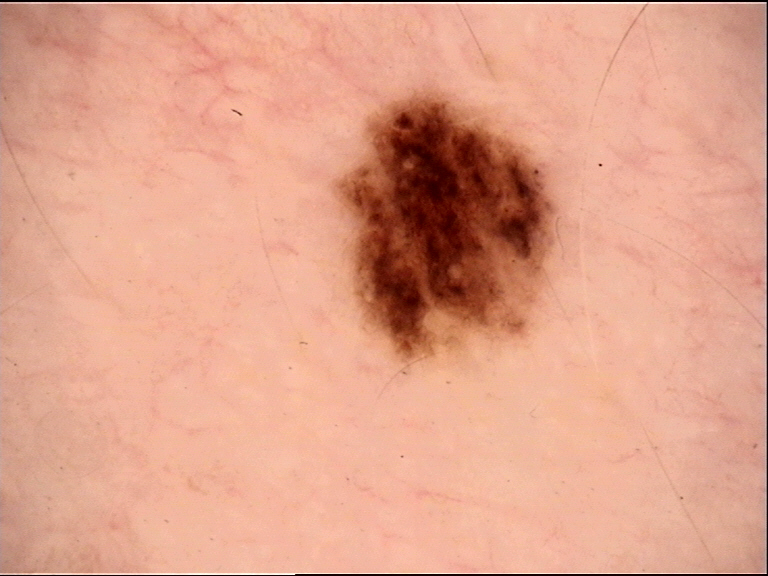image = dermoscopy, diagnostic label = dysplastic junctional nevus (expert consensus).